A dermatoscopic image of a skin lesion.
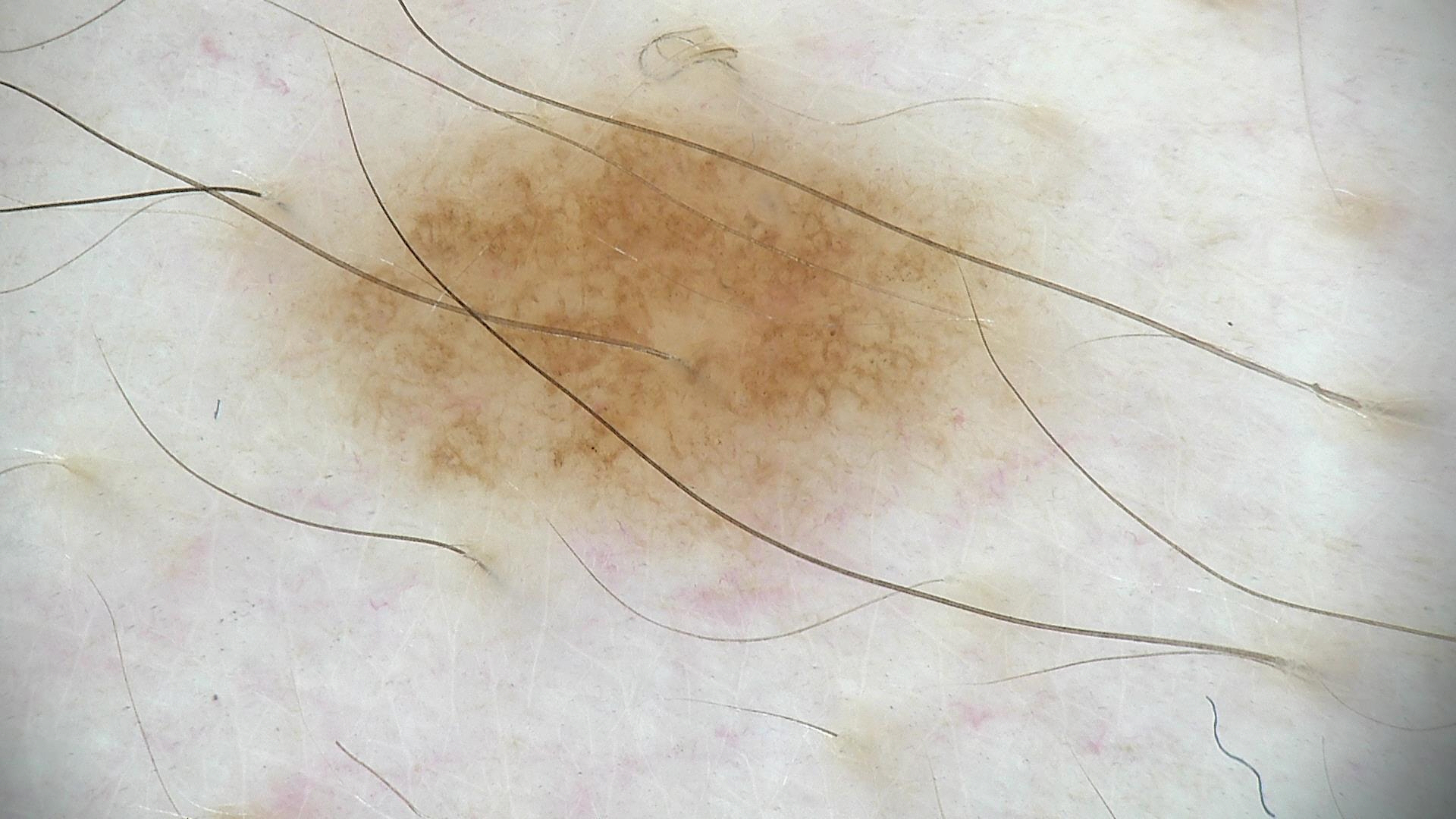{"diagnosis": {"name": "dysplastic junctional nevus", "code": "jd", "malignancy": "benign", "super_class": "melanocytic", "confirmation": "expert consensus"}}